Dermoscopy of a skin lesion:
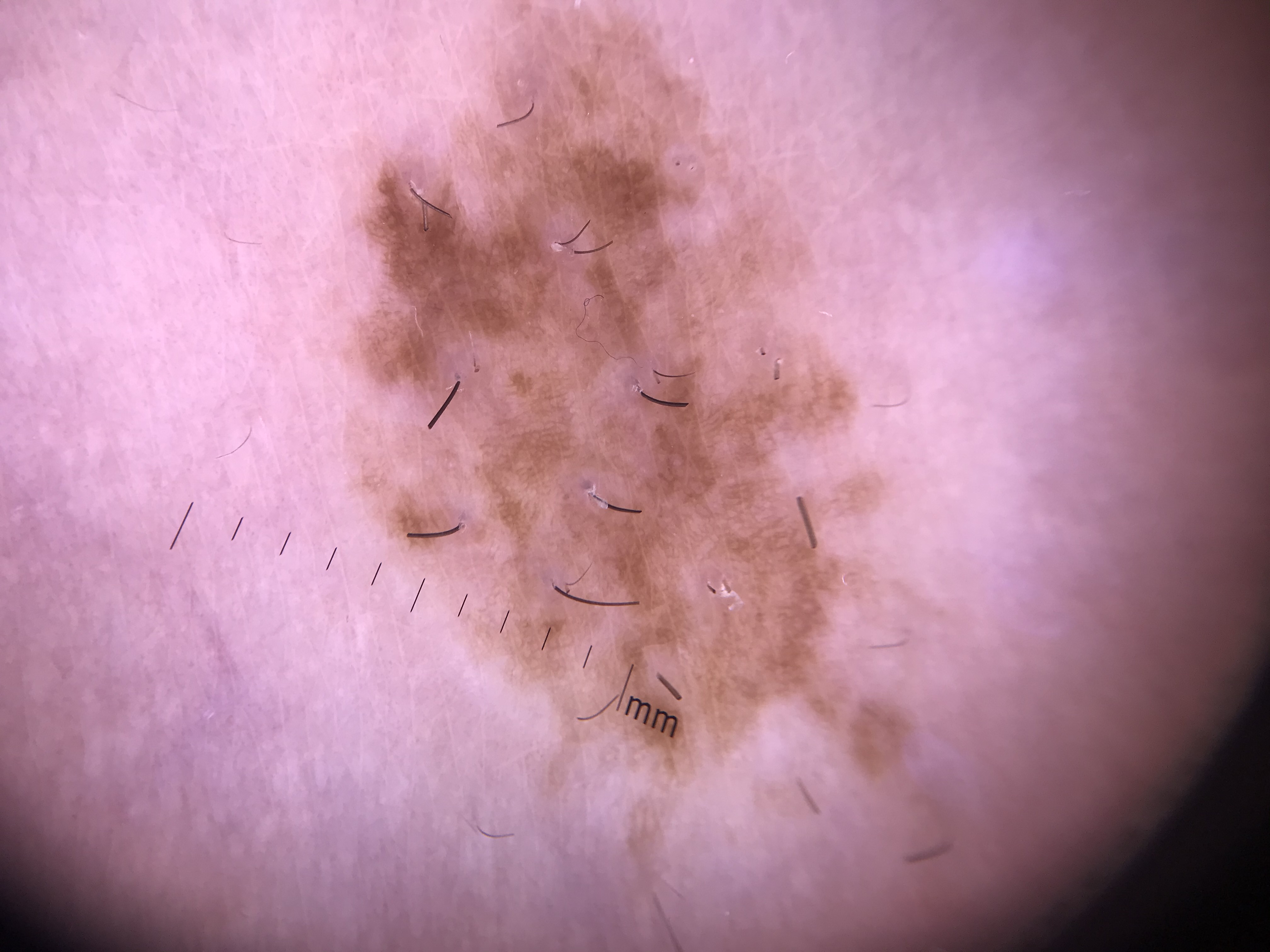<dermoscopy>
<lesion_type>
<main_class>banal</main_class>
<pattern>compound</pattern>
</lesion_type>
<diagnosis>
<name>congenital compound nevus</name>
<code>ccb</code>
<malignancy>benign</malignancy>
<super_class>melanocytic</super_class>
<confirmation>expert consensus</confirmation>
</diagnosis>
</dermoscopy>